A skin lesion imaged with a dermatoscope.
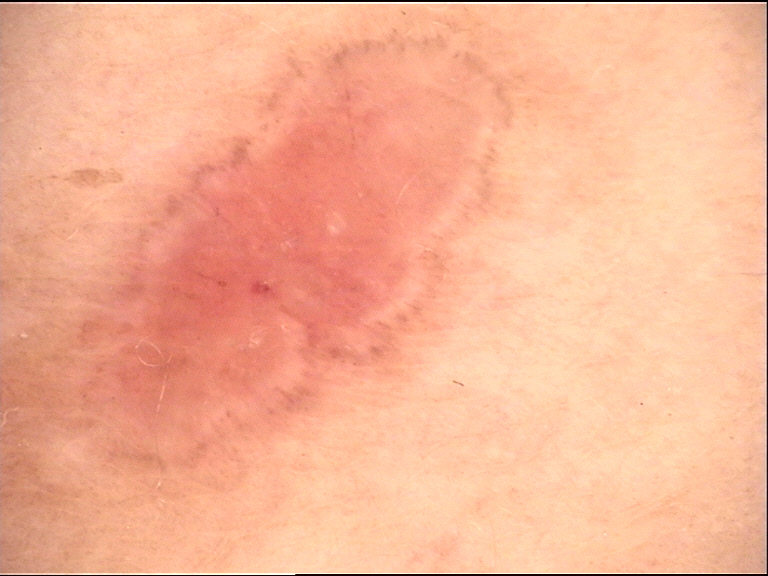classification=keratinocytic
class=basal cell carcinoma (biopsy-proven)